The affected area is the arm, palm, back of the hand, top or side of the foot and sole of the foot. The photograph is a close-up of the affected area — 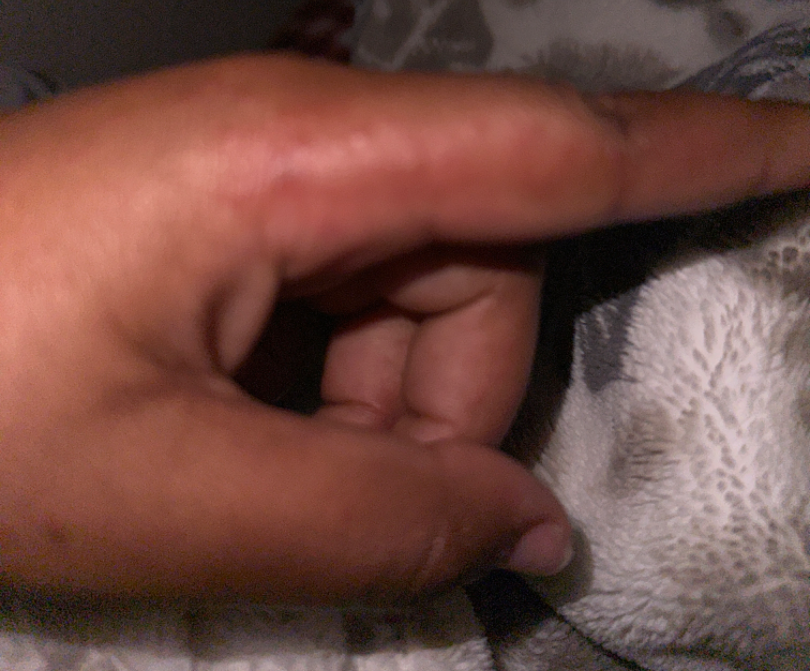Review: The reviewer was unable to grade this case for skin condition. Patient information: The lesion is described as raised or bumpy and fluid-filled. The patient considered this a rash. The condition has been present for about one day. Symptoms reported: enlargement, bothersome appearance, itching and pain.